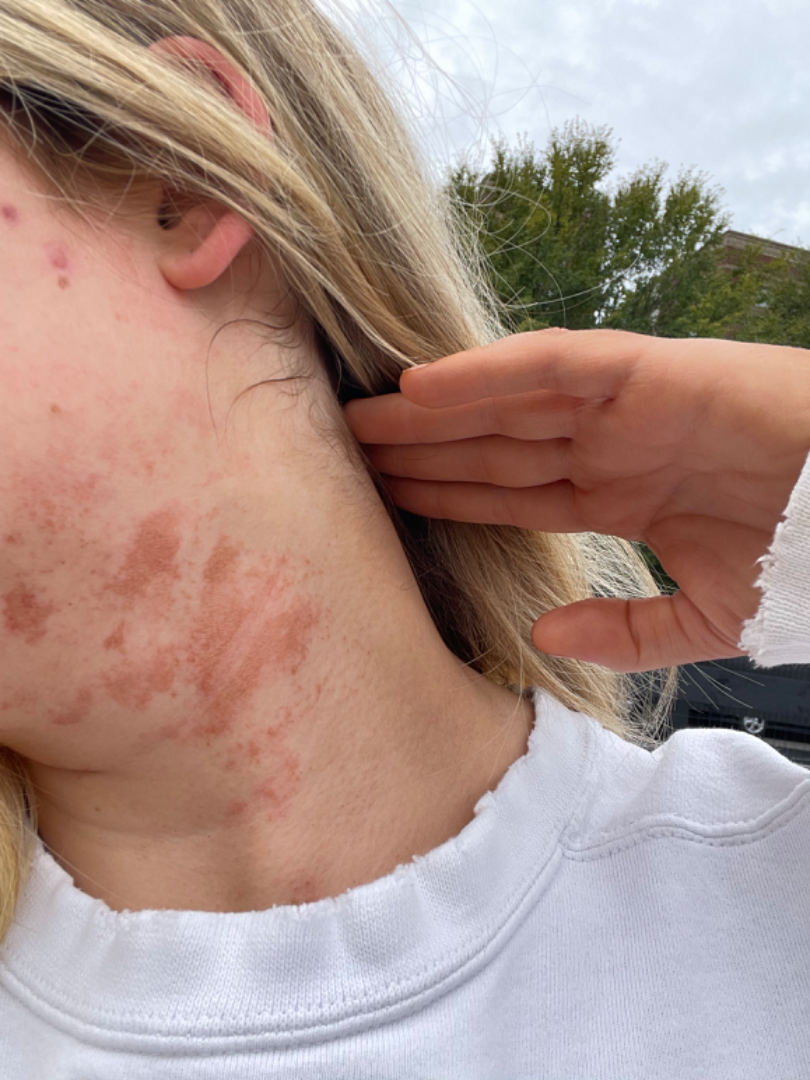Notes:
• diagnostic considerations — the leading impression is Eczema; an alternative is ecchymoses